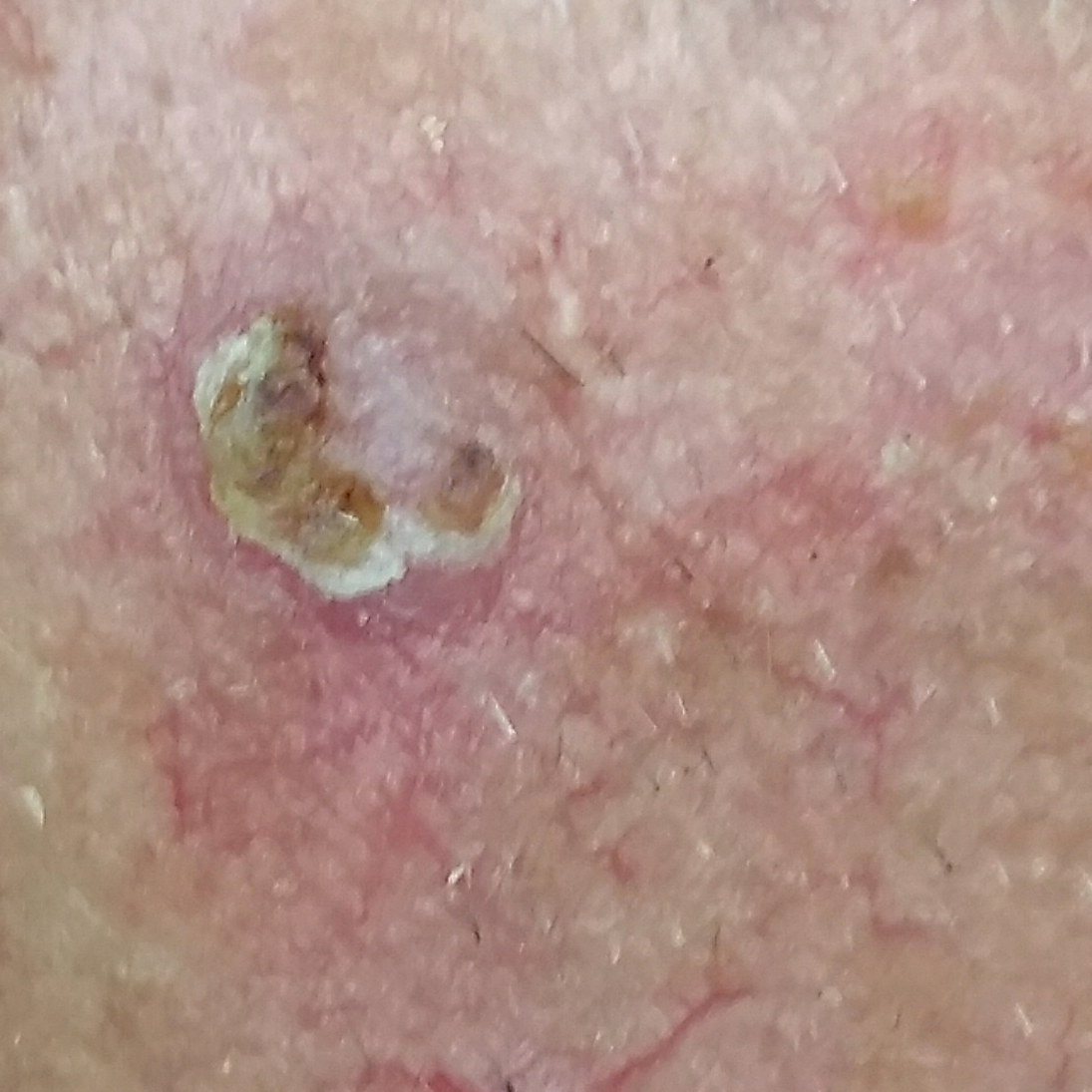Findings:
A clinical close-up photograph of a skin lesion. Recorded as Fitzpatrick skin type II. History notes prior skin cancer (patient or family) and no tobacco use. A male patient 77 years of age. The lesion was found on an ear. By the patient's account, the lesion has bled, itches, and hurts, but has not changed and is not elevated.
Conclusion:
Histopathologically confirmed as a basal cell carcinoma.